A dermoscopic image of a skin lesion; the patient was assessed as skin type II; a male patient approximately 45 years of age.
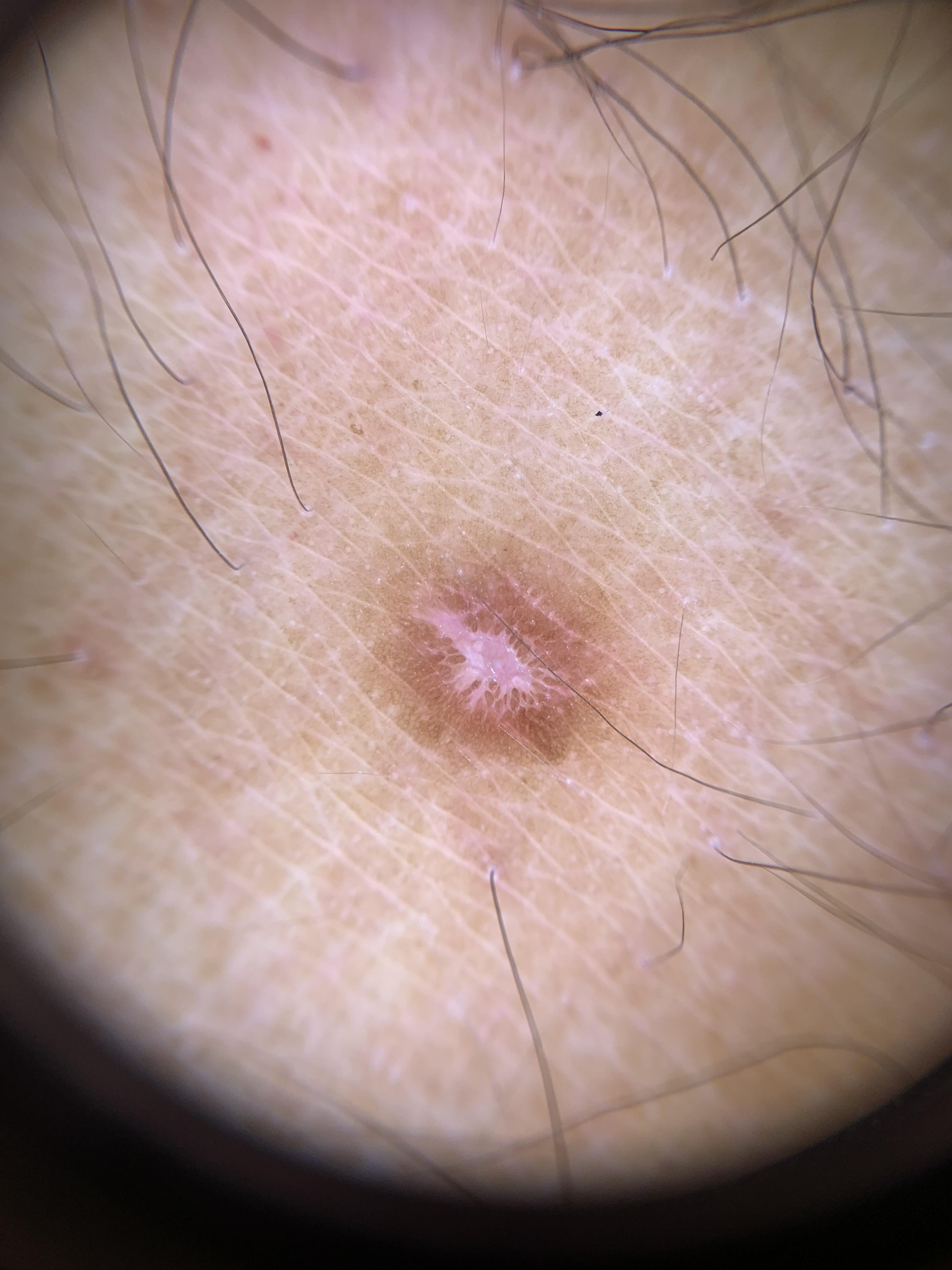anatomic site: a lower extremity, diagnostic label: Dermatofibroma (clinical impression).